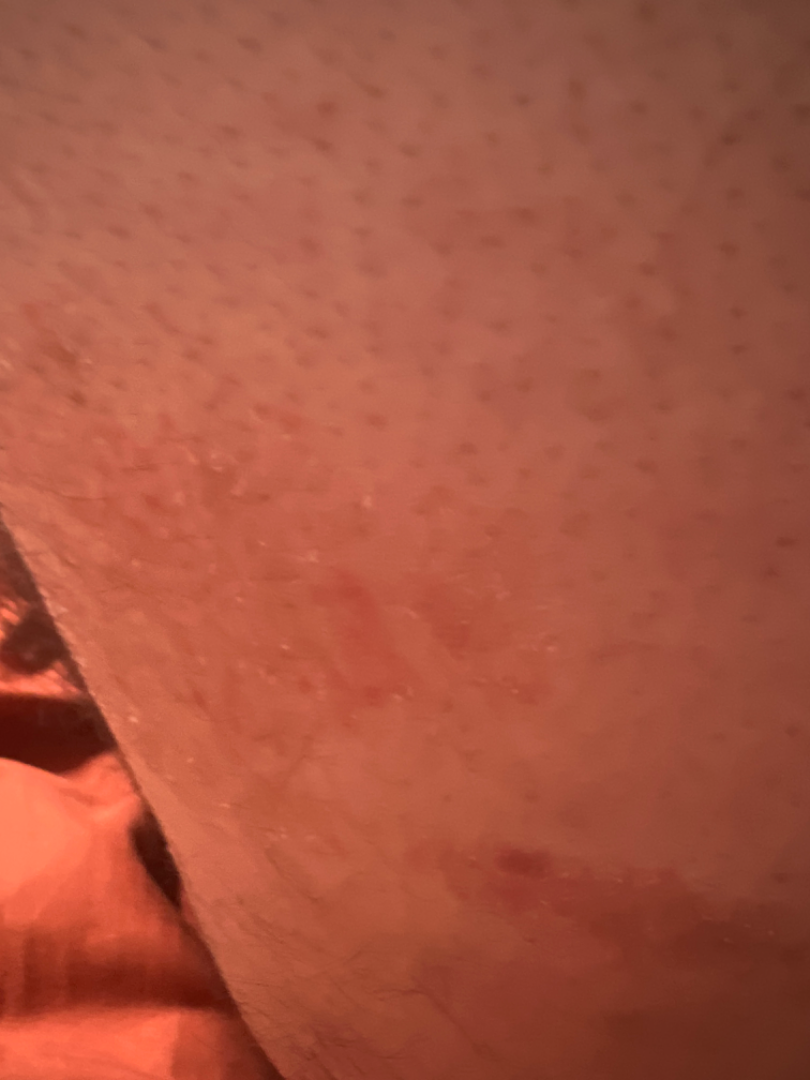Clinical context:
Fitzpatrick II; non-clinician graders estimated a Monk Skin Tone of 2. An image taken at an angle.
Assessment:
On teledermatology review: the leading impression is Tinea; also on the differential is Psoriasis; an alternative is Eczema.